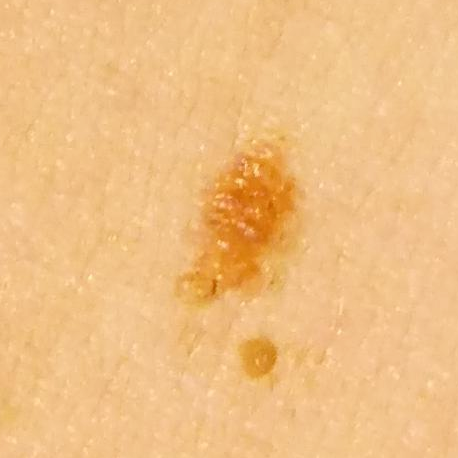Summary: A clinical close-up photograph of a skin lesion. A patient age 31. The lesion is on the back. Per patient report, the lesion is elevated and has grown. Impression: Consistent with a nevus.